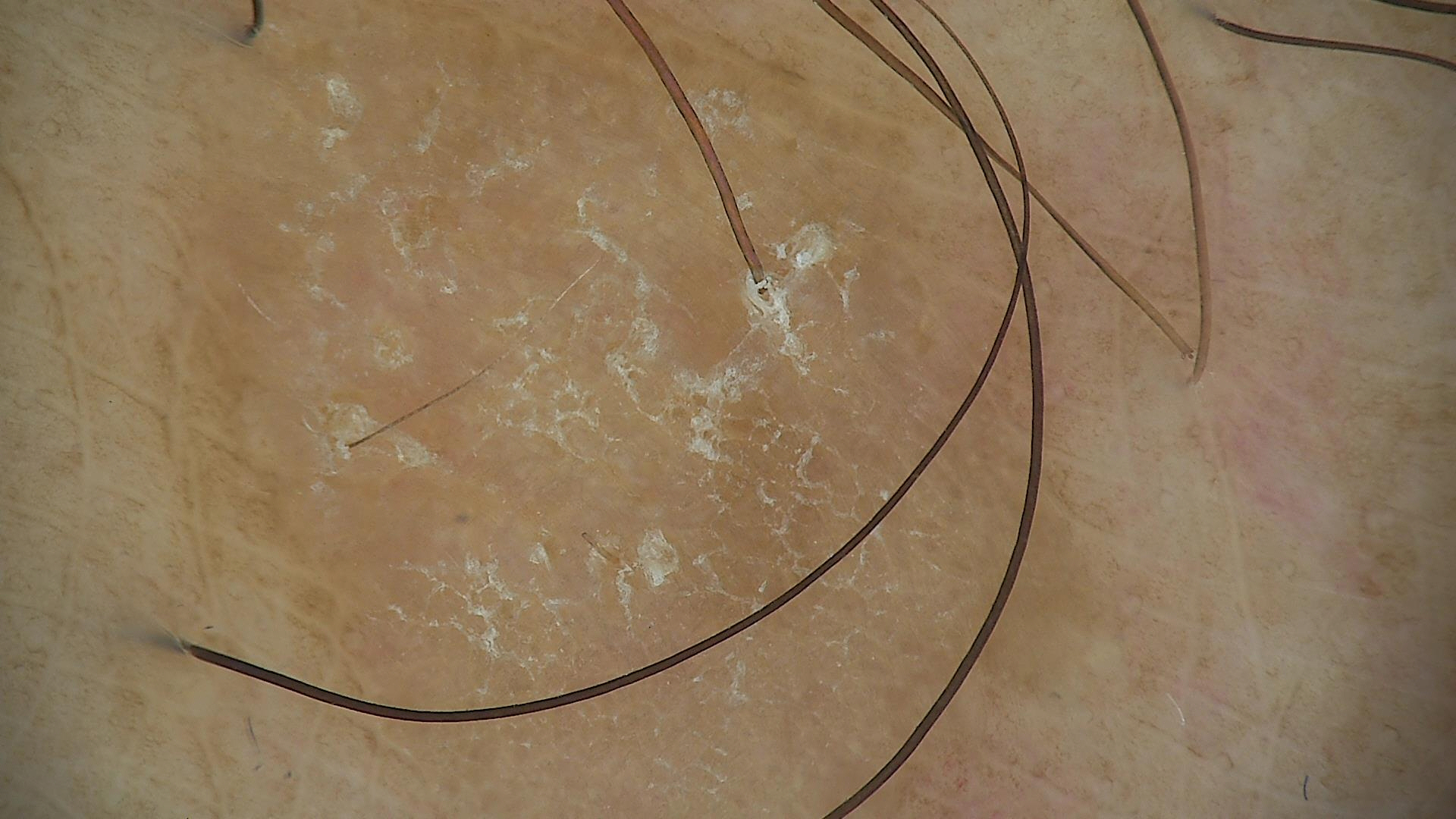The architecture is that of a fibro-histiocytic lesion. The diagnostic label was a benign lesion — a dermatofibroma.